Located on the leg; close-up view:
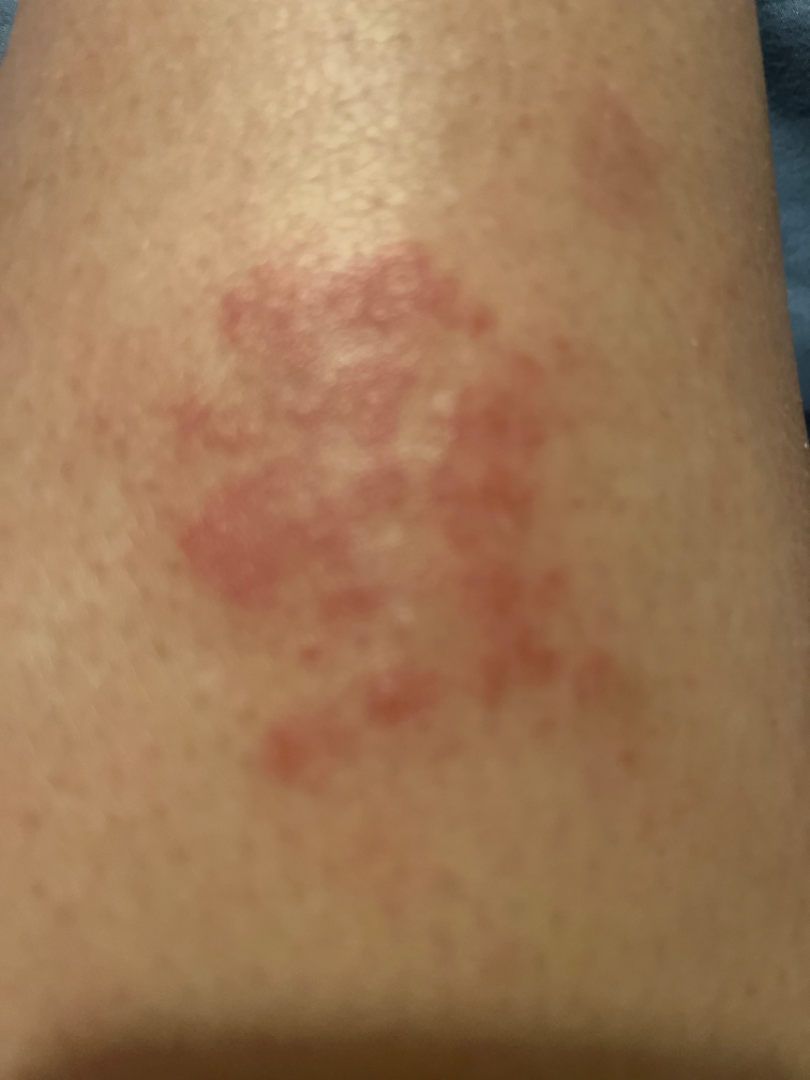The image was not sufficient for the reviewer to characterize the skin condition.